Dermoscopy of a skin lesion.
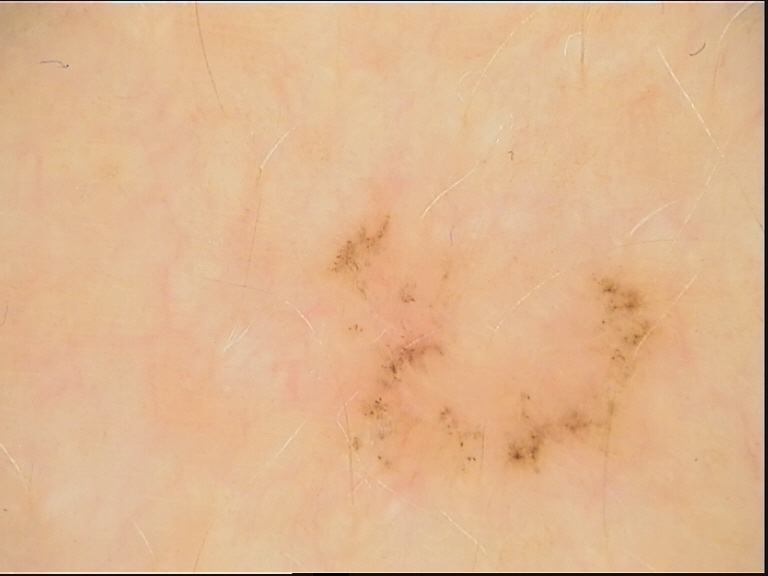subtype — keratinocytic; diagnostic label — basal cell carcinoma (biopsy-proven).